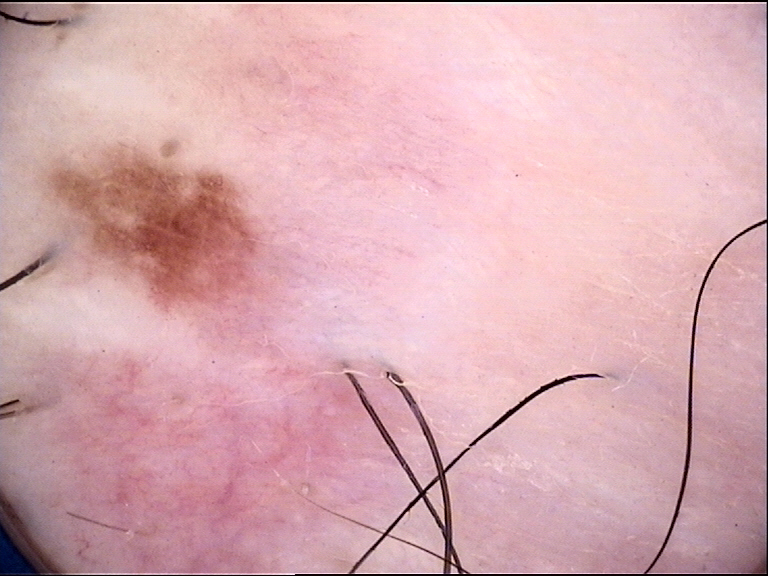A dermatoscopic image of a skin lesion.
The diagnosis was a dysplastic junctional nevus.